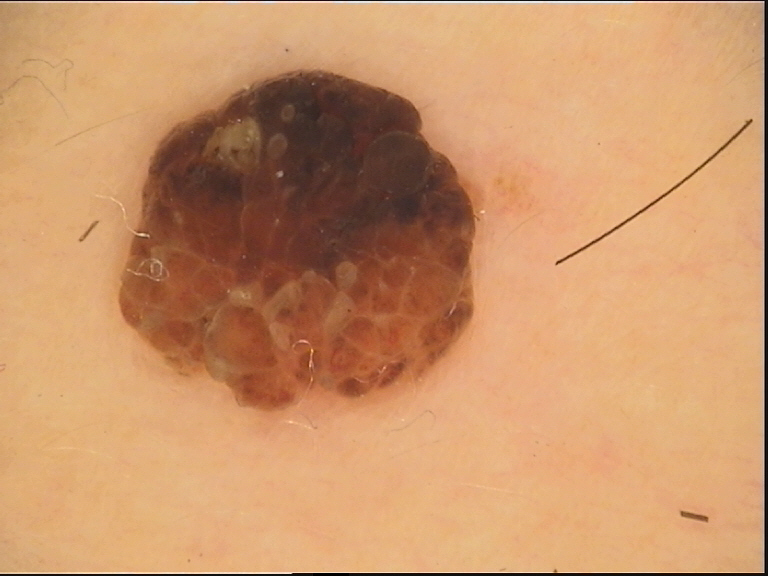Findings:
A dermoscopic close-up of a skin lesion.
Conclusion:
Labeled as a compound nevus.